A skin lesion imaged with a dermatoscope — 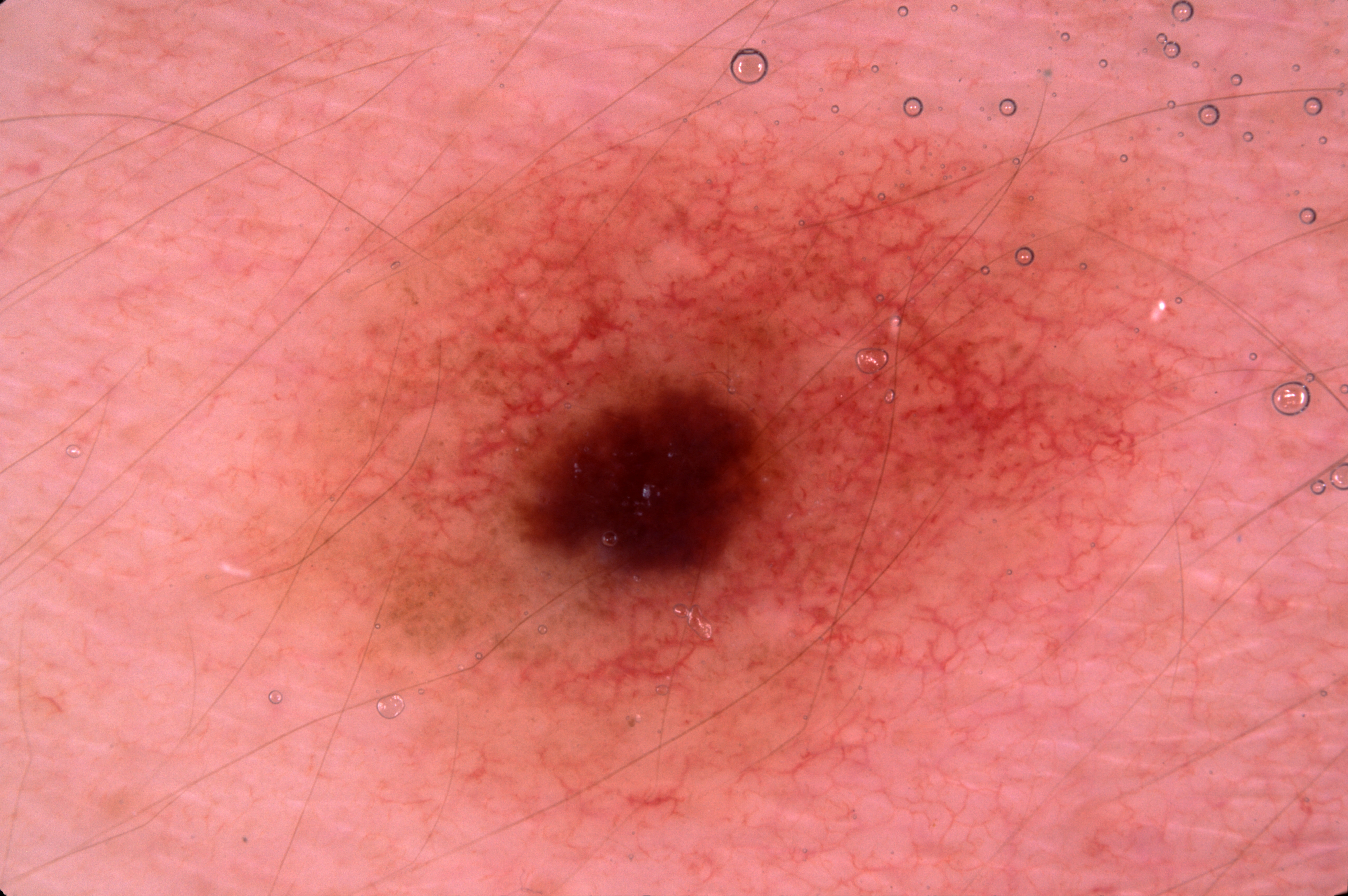{"dermoscopic_features": {"present": [], "absent": ["milia-like cysts", "negative network", "pigment network", "streaks"]}, "lesion_location": {"bbox_xyxy": [286, 141, 1187, 782]}, "lesion_extent": {"approx_field_fraction_pct": 27}, "diagnosis": {"name": "melanocytic nevus", "malignancy": "benign", "lineage": "melanocytic", "provenance": "clinical"}}